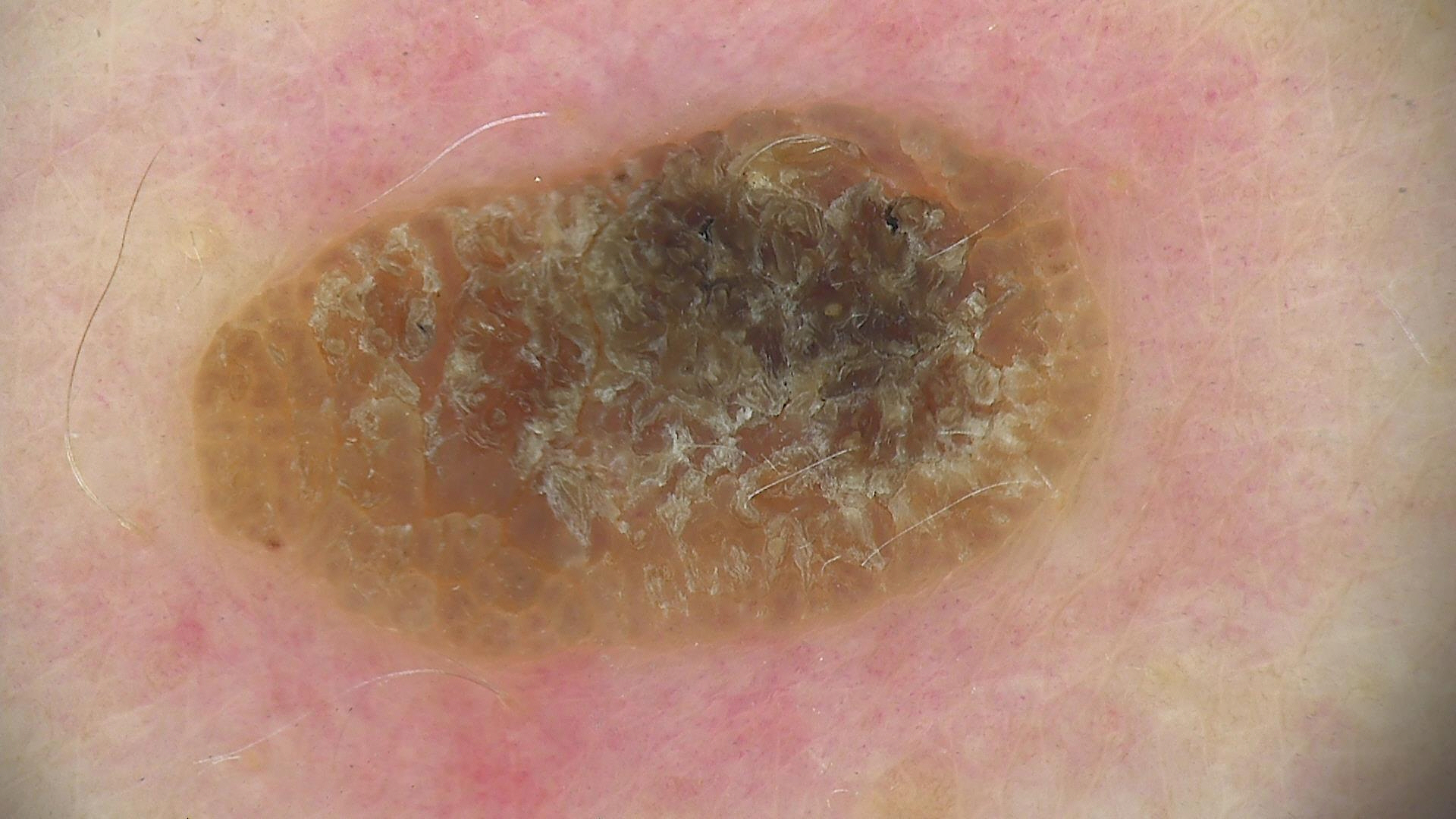image type = dermatoscopy
lesion type = keratinocytic
assessment = seborrheic keratosis (expert consensus)